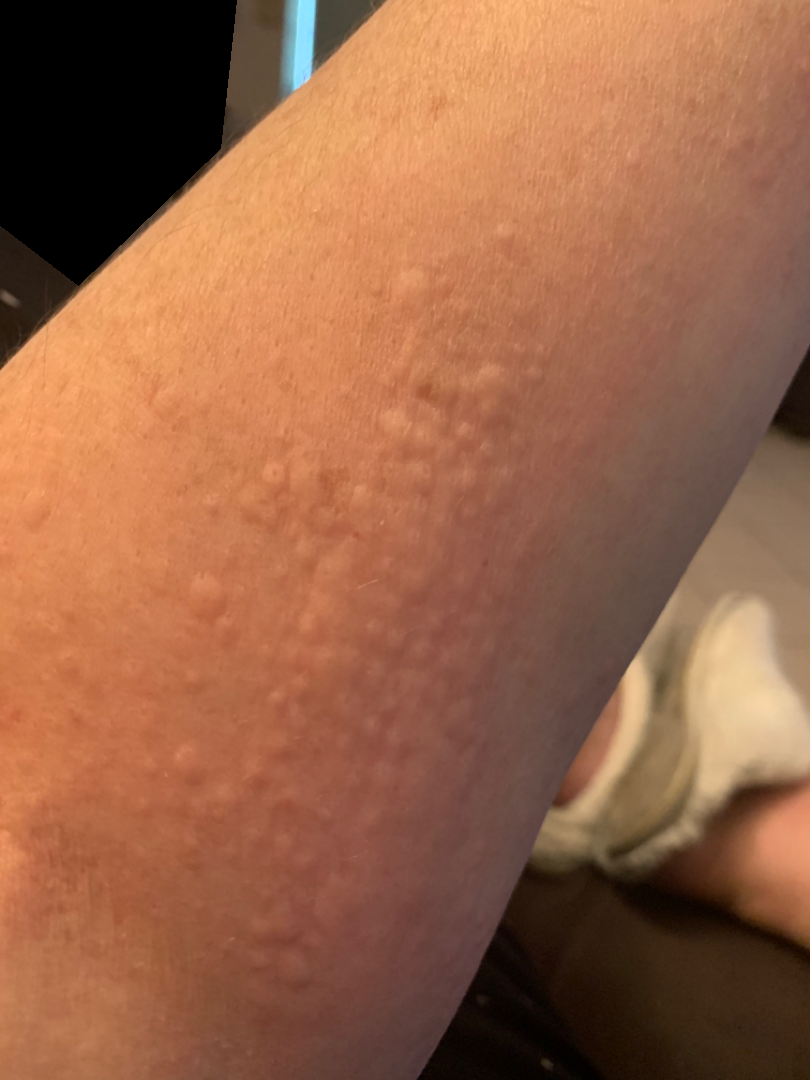Close-up view.
On remote dermatologist review, the impression was split between Urticaria and Allergic Contact Dermatitis.